By self-report, a family history of skin cancer and a personal history of cancer. A dermoscopy image of a skin lesion. Collected as part of a research study, without a referral diagnosis. The patient says their skin tans without first burning — 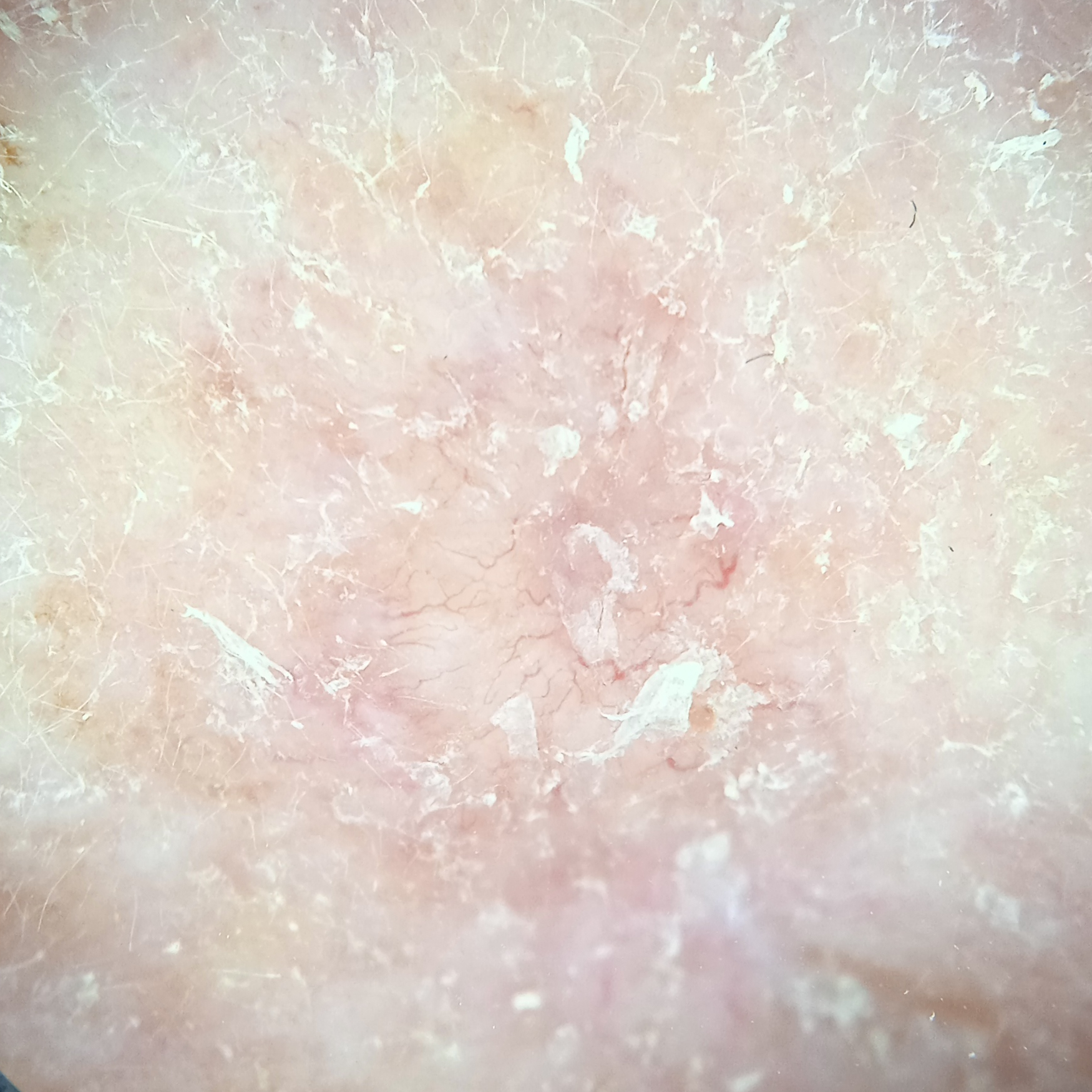Q: Where is the lesion?
A: the face
Q: How large is the lesion?
A: 7 mm
Q: What was the diagnosis?
A: basal cell carcinoma (dermatologist consensus)